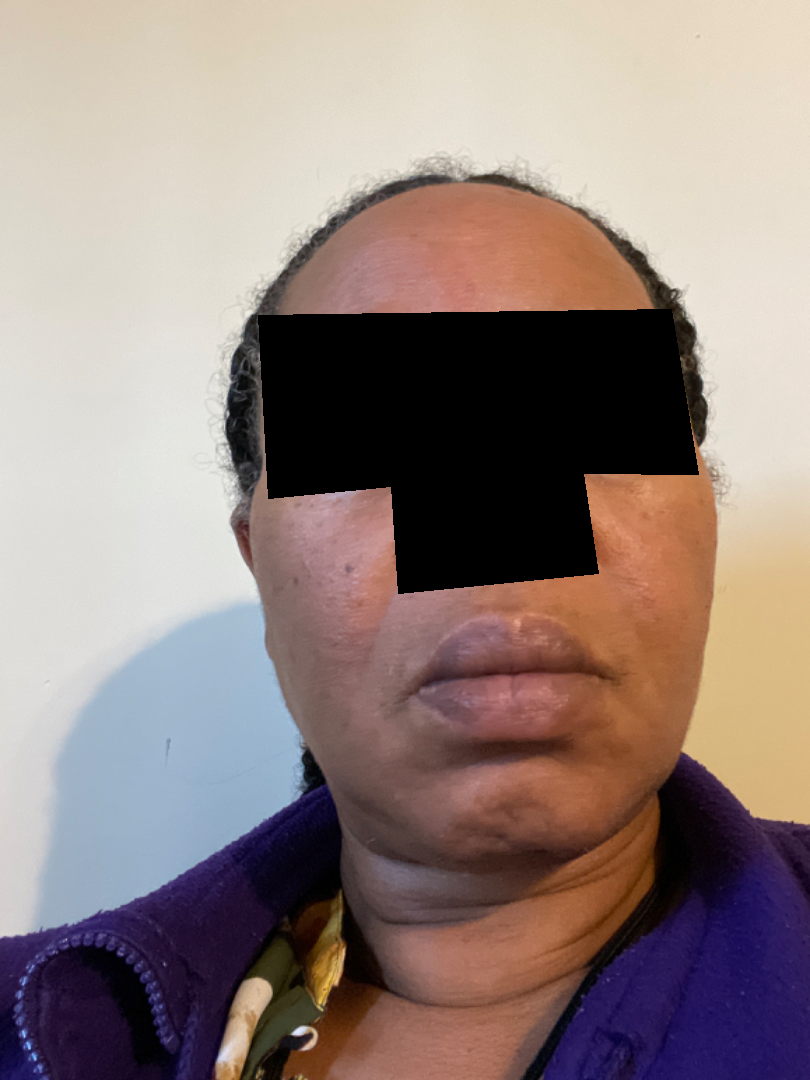The photograph is a close-up of the affected area.
The subject is 50–59, female.
On remote dermatologist review, the differential is split between Acne and Rosacea.